A skin lesion imaged with contact-polarized dermoscopy. The chart notes a first-degree relative with melanoma. Recorded as skin type III — 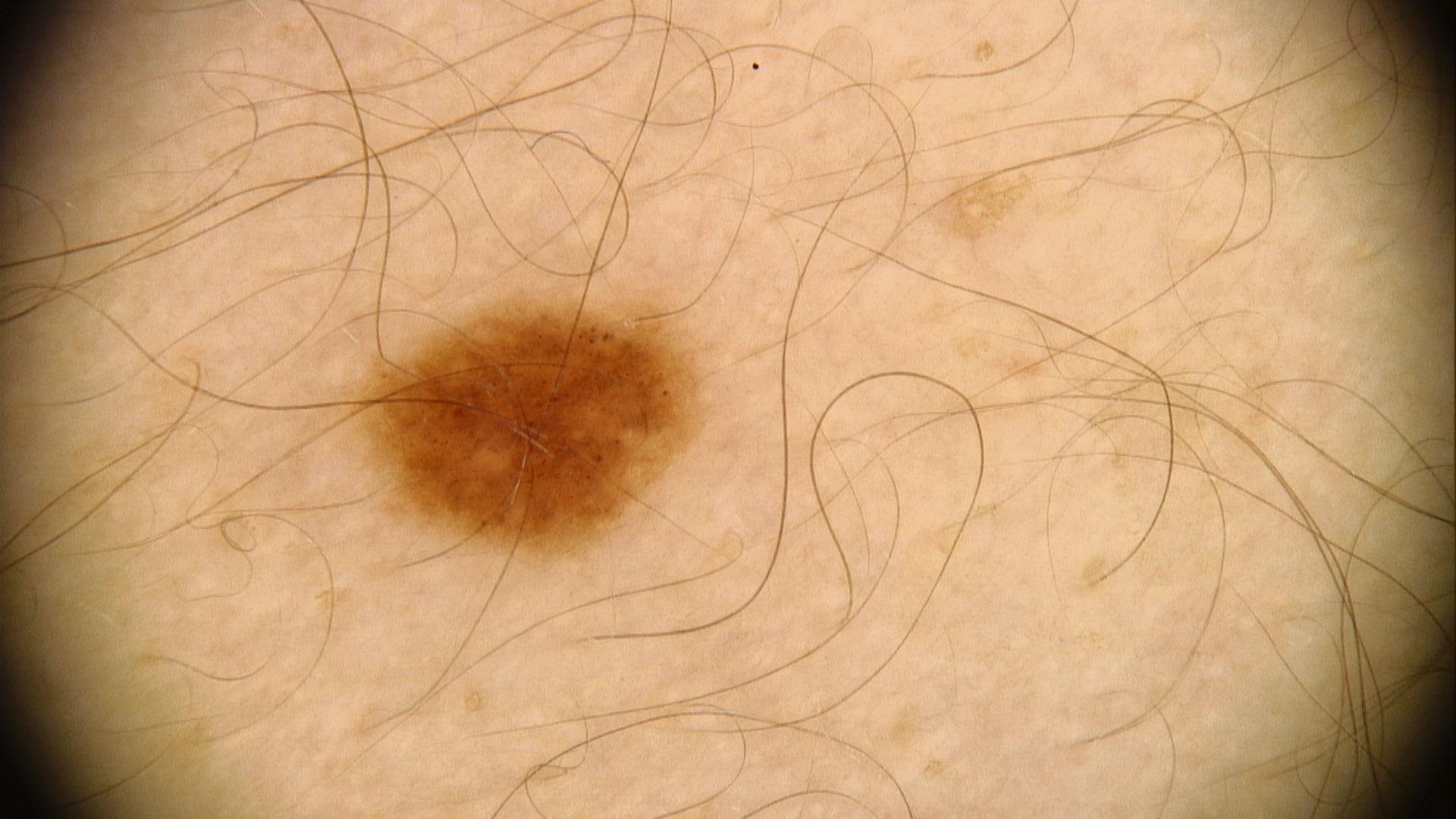lesion_location:
  region: an upper extremity
diagnosis:
  name: Nevus
  malignancy: benign
  confirmation: expert clinical impression
  lineage: melanocytic